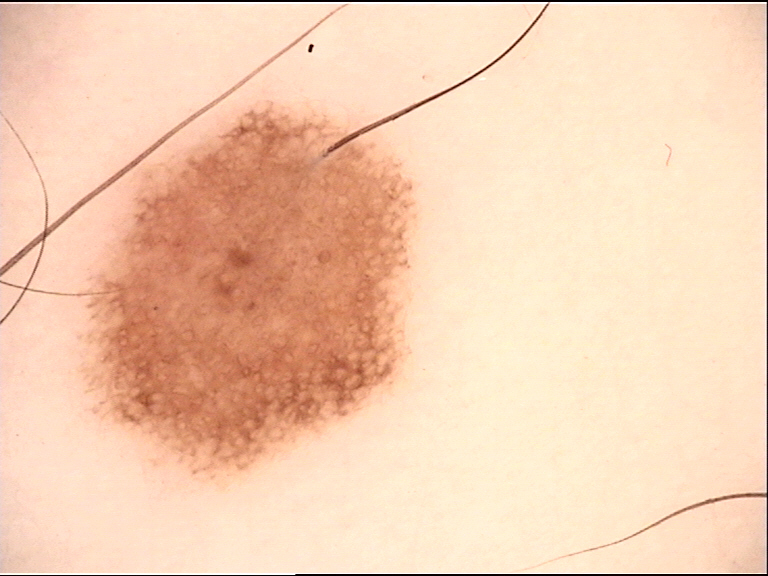Consistent with a dysplastic junctional nevus.